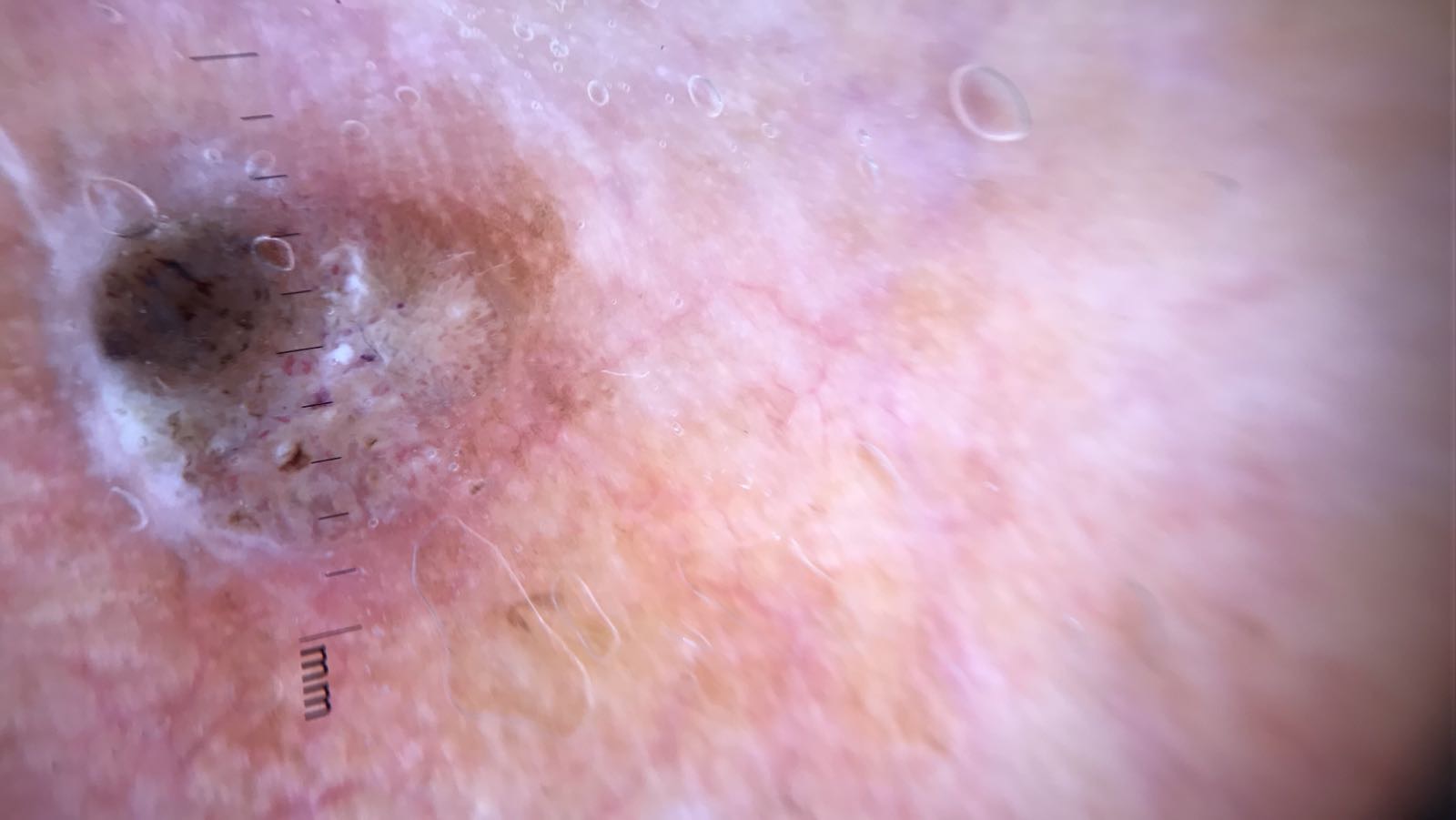<case>
<image>dermatoscopy</image>
<lesion_type>
<main_class>keratinocytic</main_class>
</lesion_type>
<diagnosis>
<name>seborrheic keratosis</name>
<code>sk</code>
<malignancy>benign</malignancy>
<super_class>non-melanocytic</super_class>
<confirmation>expert consensus</confirmation>
</diagnosis>
</case>